A dermatoscopic image of a skin lesion.
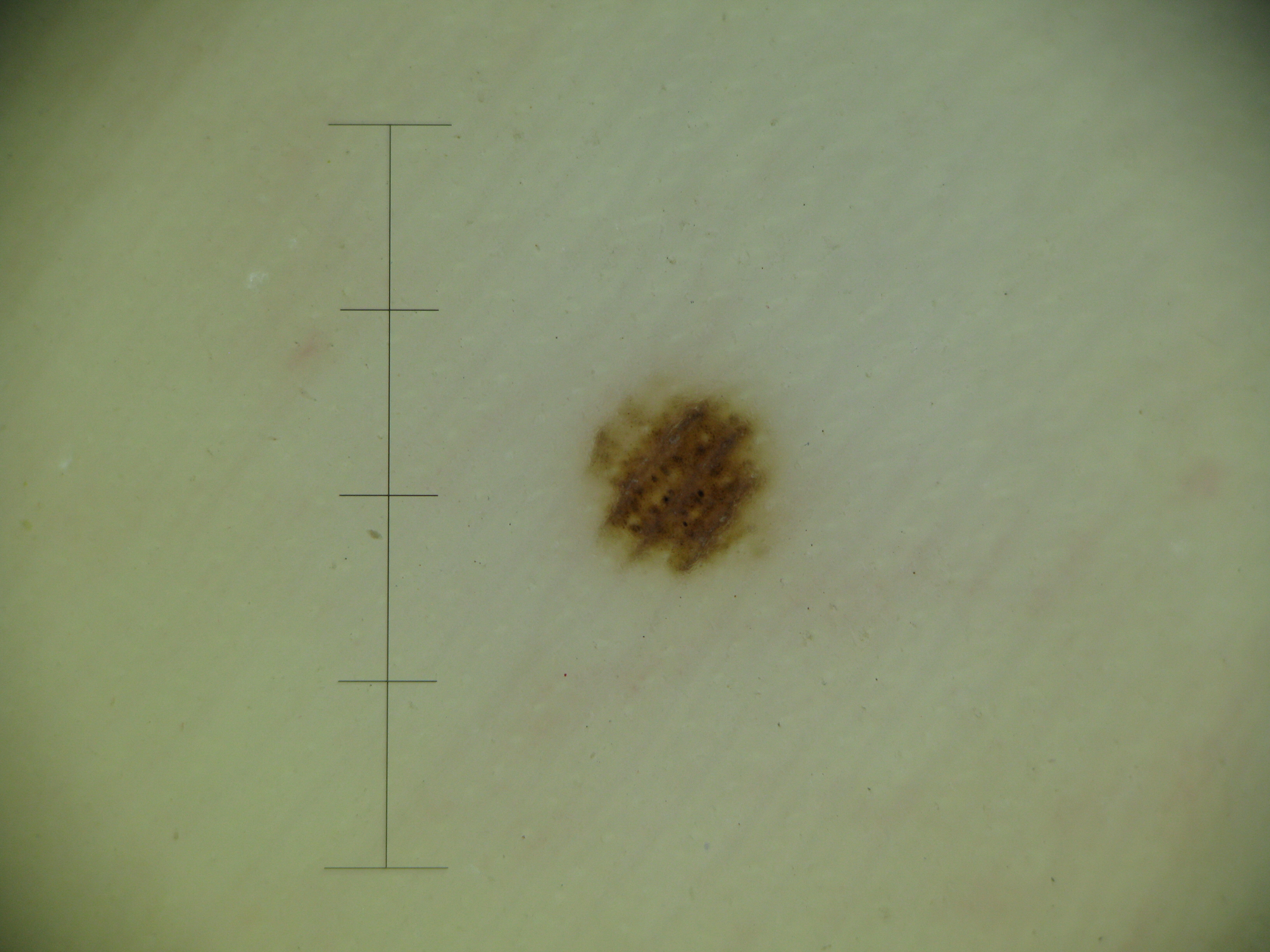classification: banal
assessment: acral junctional nevus (expert consensus)